A dermoscopy image of a single skin lesion: 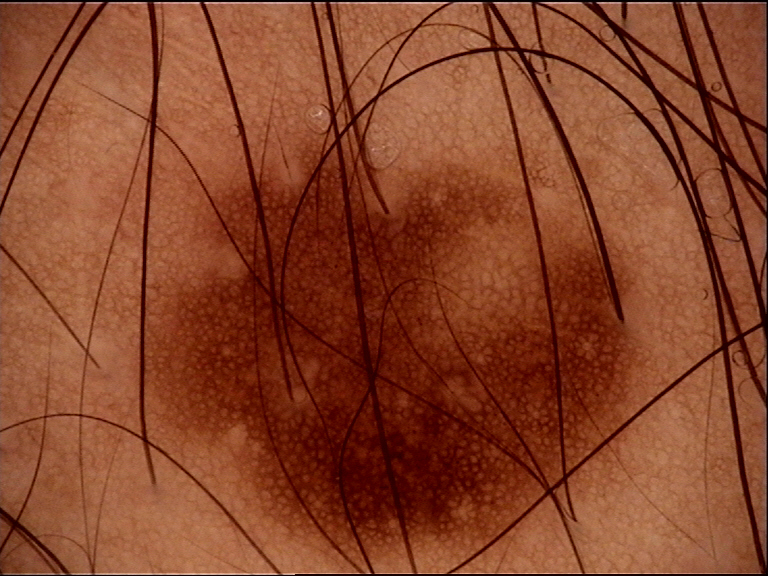Q: What is this lesion?
A: junctional nevus (expert consensus)